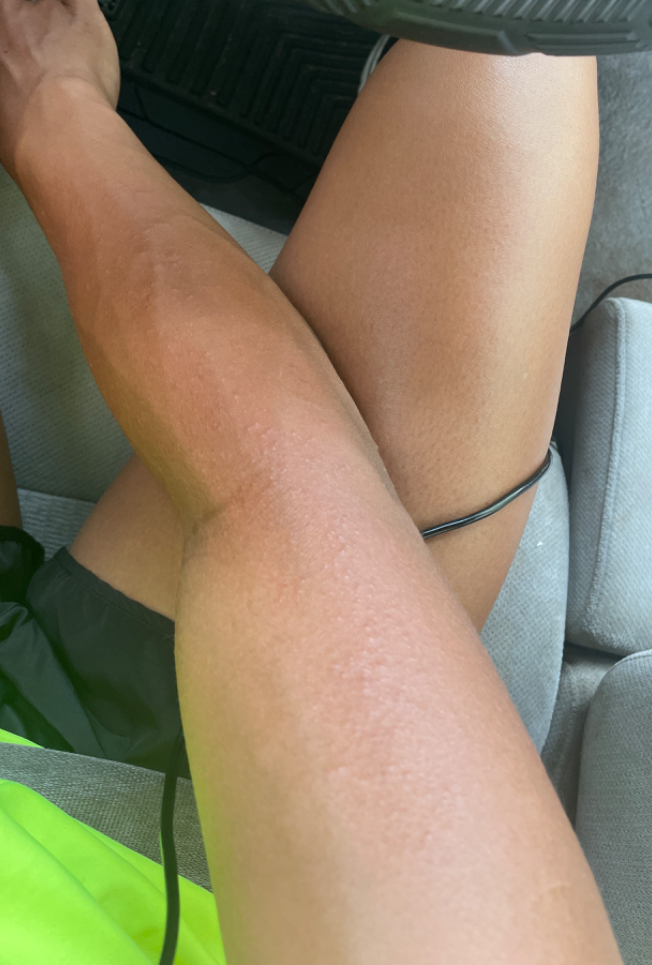History:
The lesion is described as raised or bumpy. Skin tone: Fitzpatrick IV; lay graders estimated a Monk Skin Tone of 4. The photograph was taken at a distance. The affected area is the arm and head or neck. The contributor reports the condition has been present for one to four weeks.
Impression:
Reviewed remotely by one dermatologist: favoring Eczema; also consider Lichen nitidus; with consideration of Allergic Contact Dermatitis.